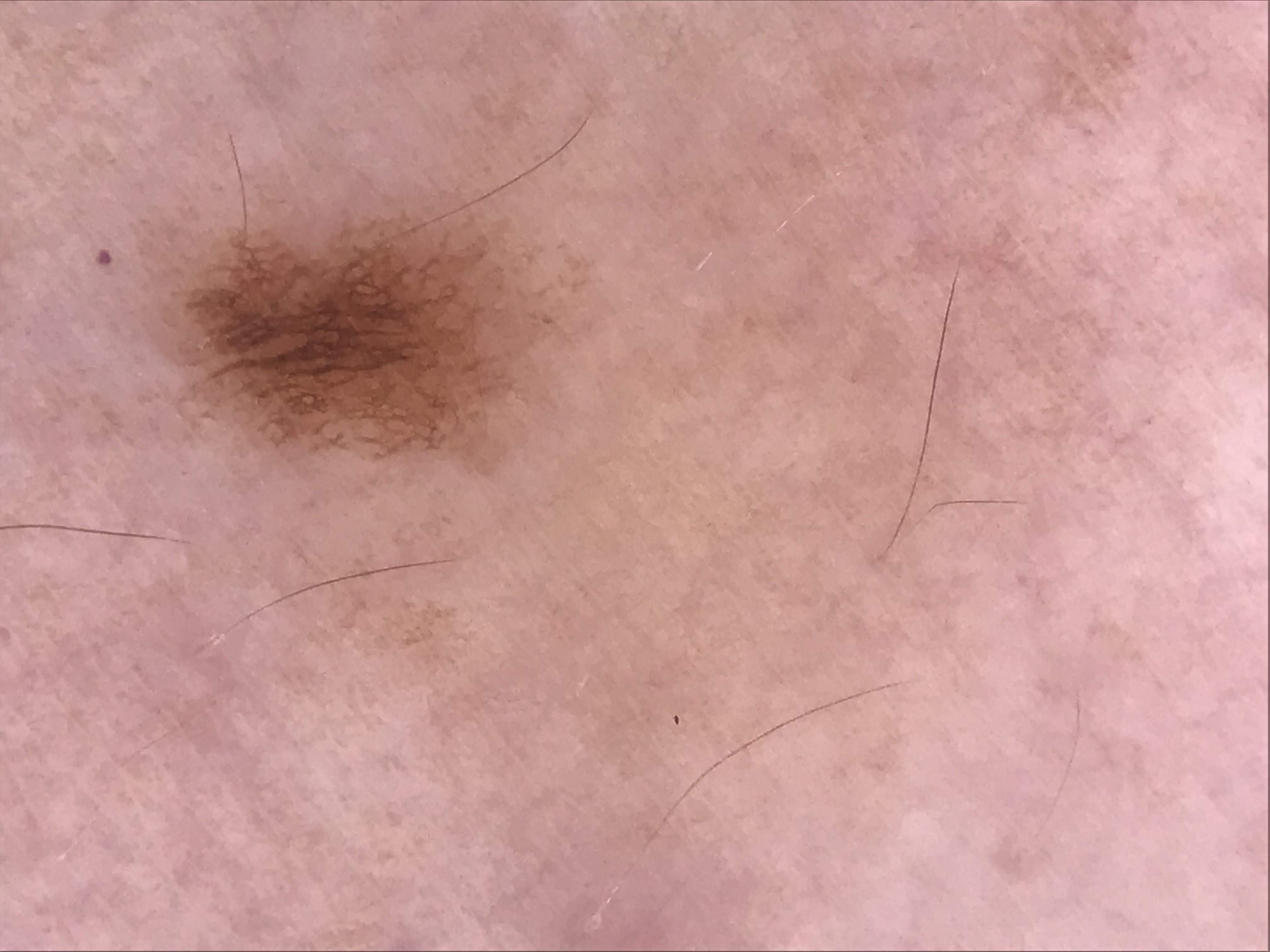Conclusion: The diagnostic label was a dysplastic junctional nevus.